A close-up photograph · the leg and arm are involved.
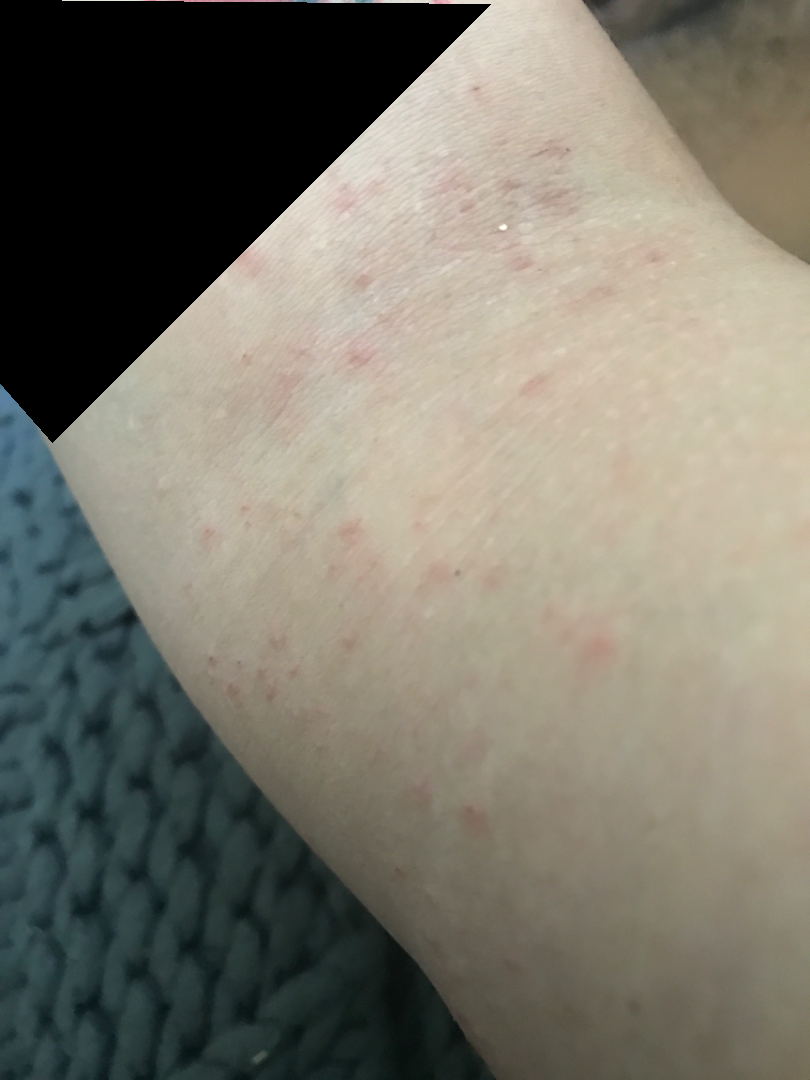Patient information:
The patient reports itching. The patient described the issue as a rash. The lesion is described as raised or bumpy. The patient reports the condition has been present for less than one week.
Review:
On remote dermatologist review, the reviewer's impression was Eczema.